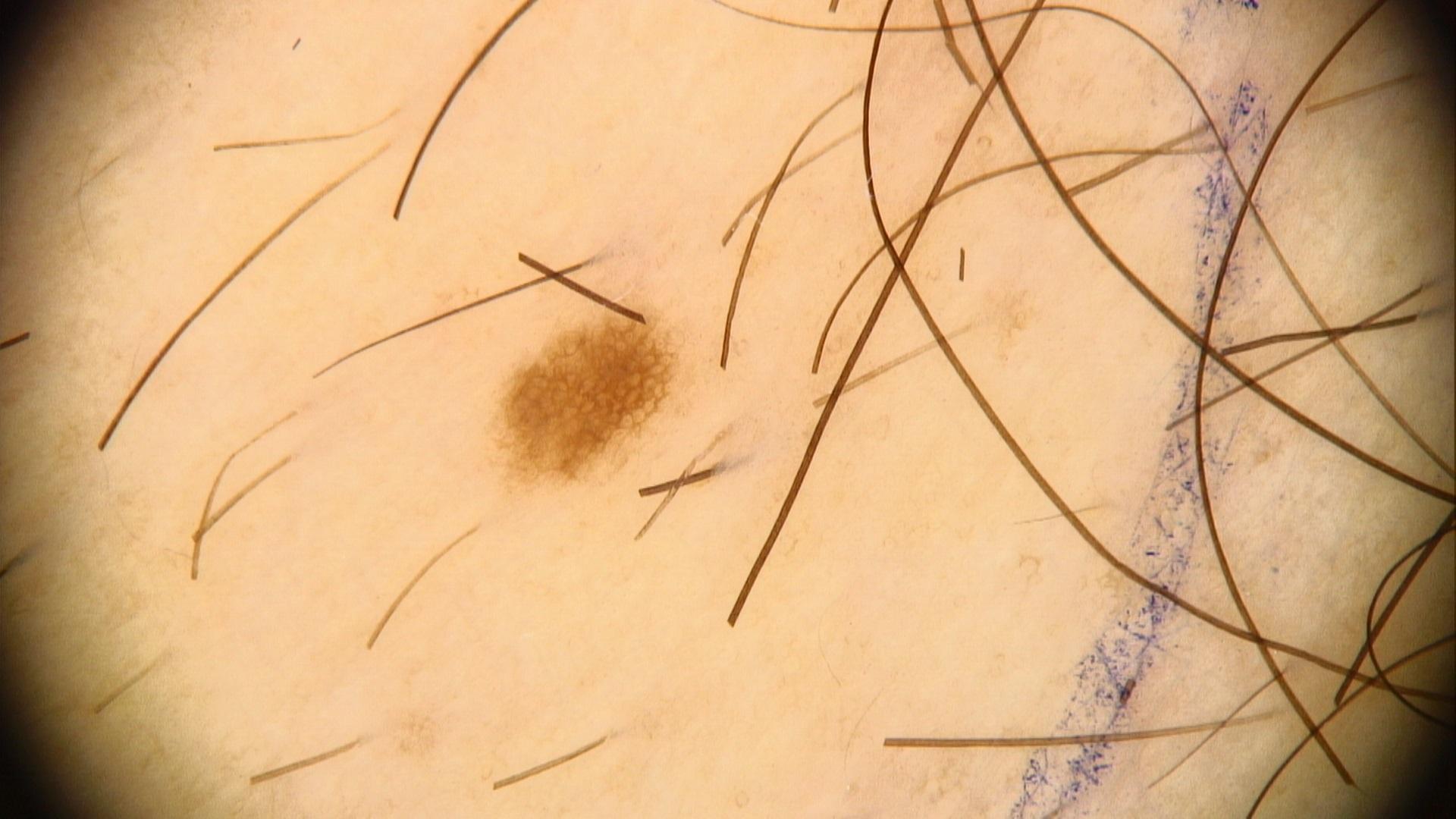A skin lesion imaged with contact-polarized dermoscopy. The diagnostic impression was a benign, melanocytic lesion — a nevus.